Recorded as FST II; dermoscopy of a skin lesion; a female patient aged 73-77.
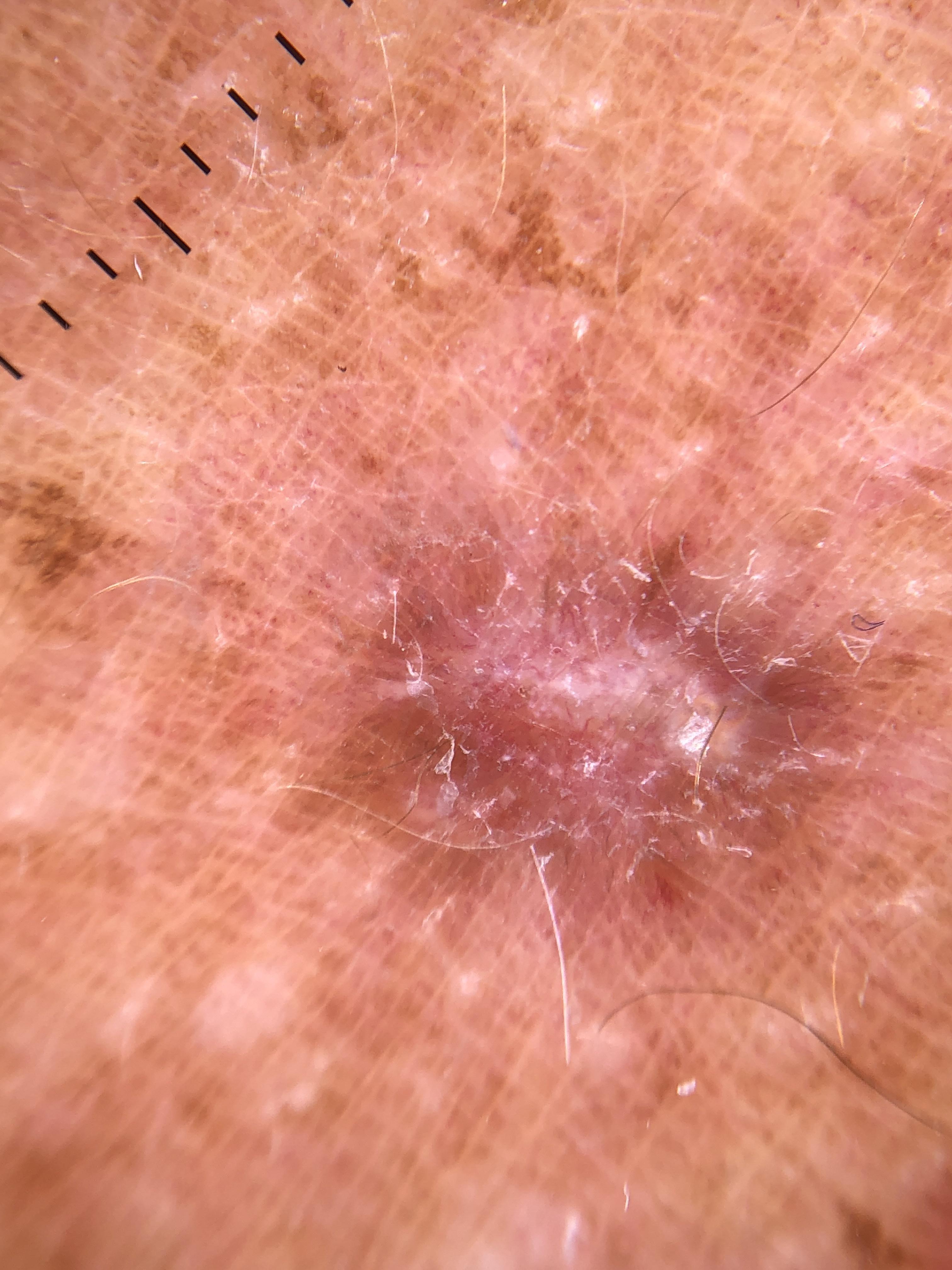| feature | finding |
|---|---|
| diagnostic label | Squamous cell carcinoma (biopsy-proven) |